Dermoscopy of a skin lesion: 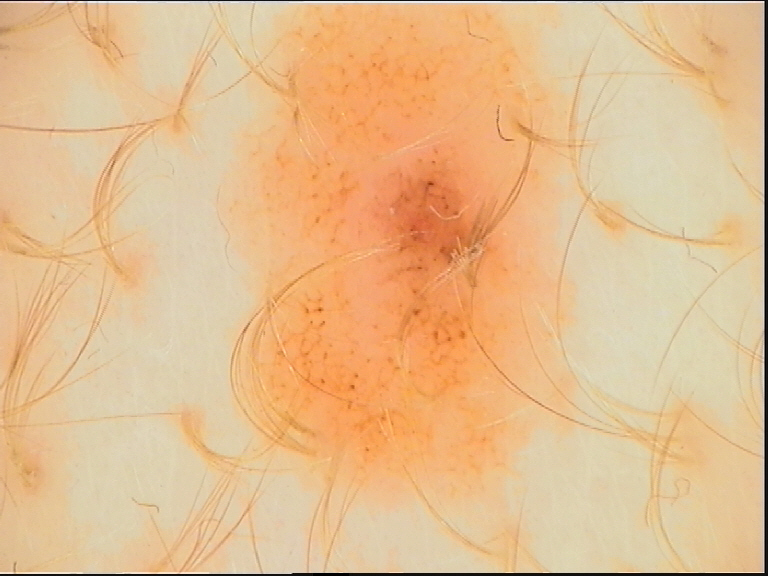Findings: The morphology is that of a banal lesion. Conclusion: Consistent with a compound nevus.